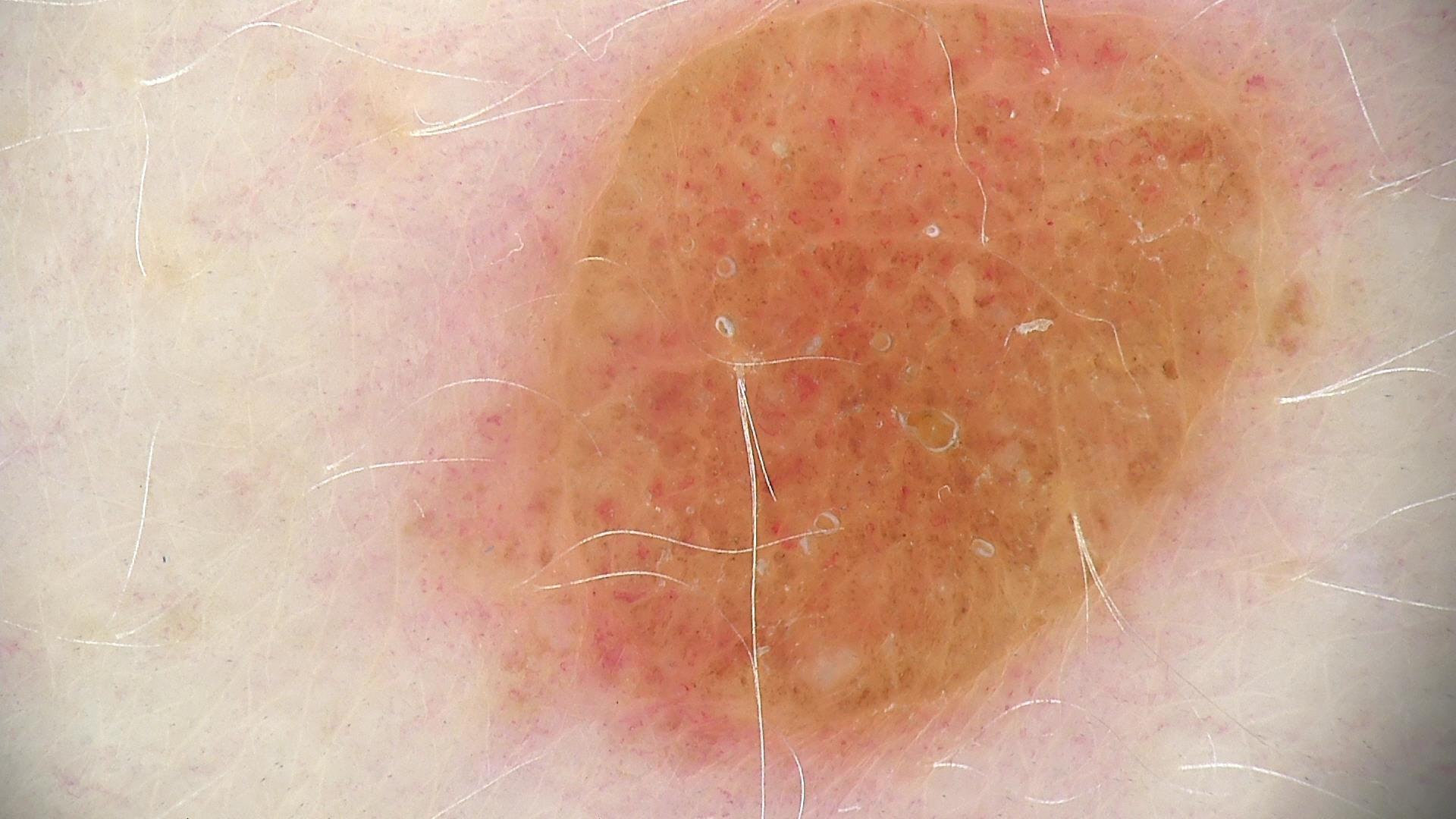image = dermoscopy; lesion type = banal; label = compound nevus (expert consensus).